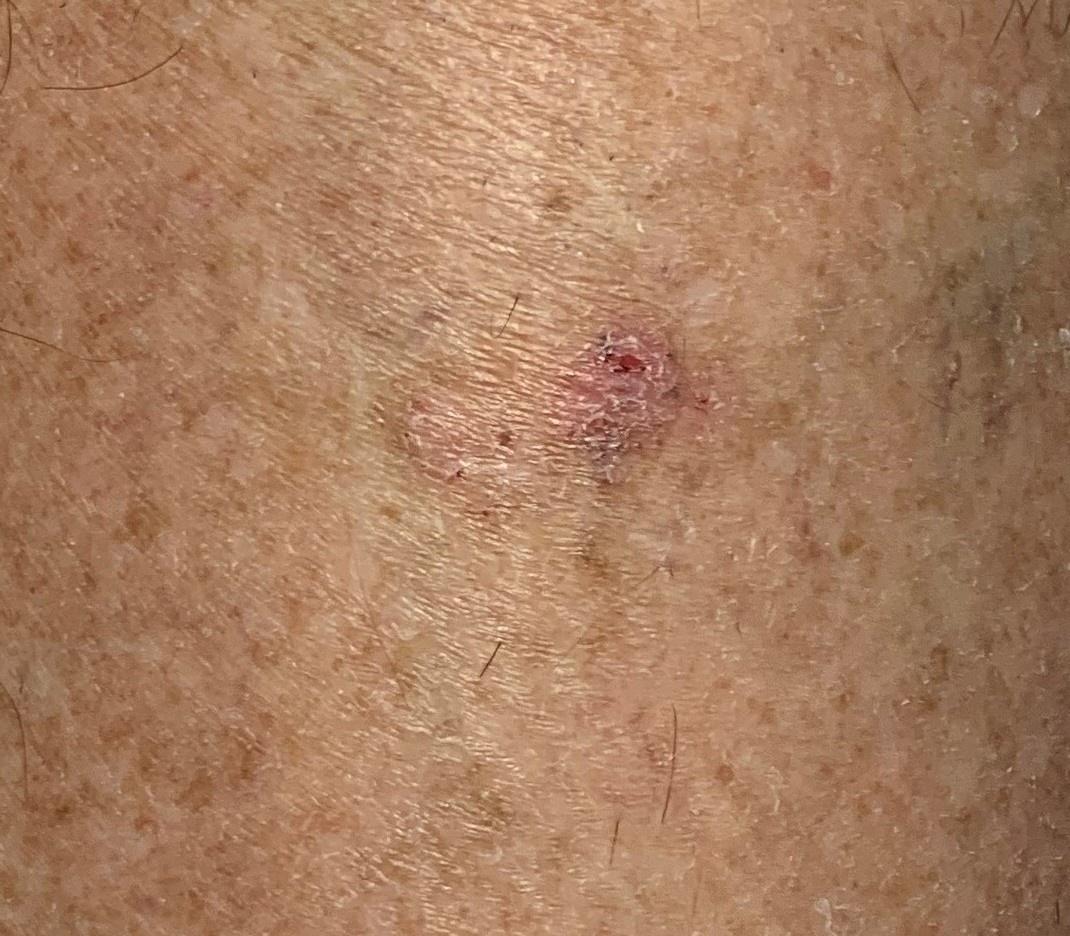Case summary: A male patient aged 78-82. The lesion is located on a lower extremity. Conclusion: Histopathology confirmed a basal cell carcinoma.